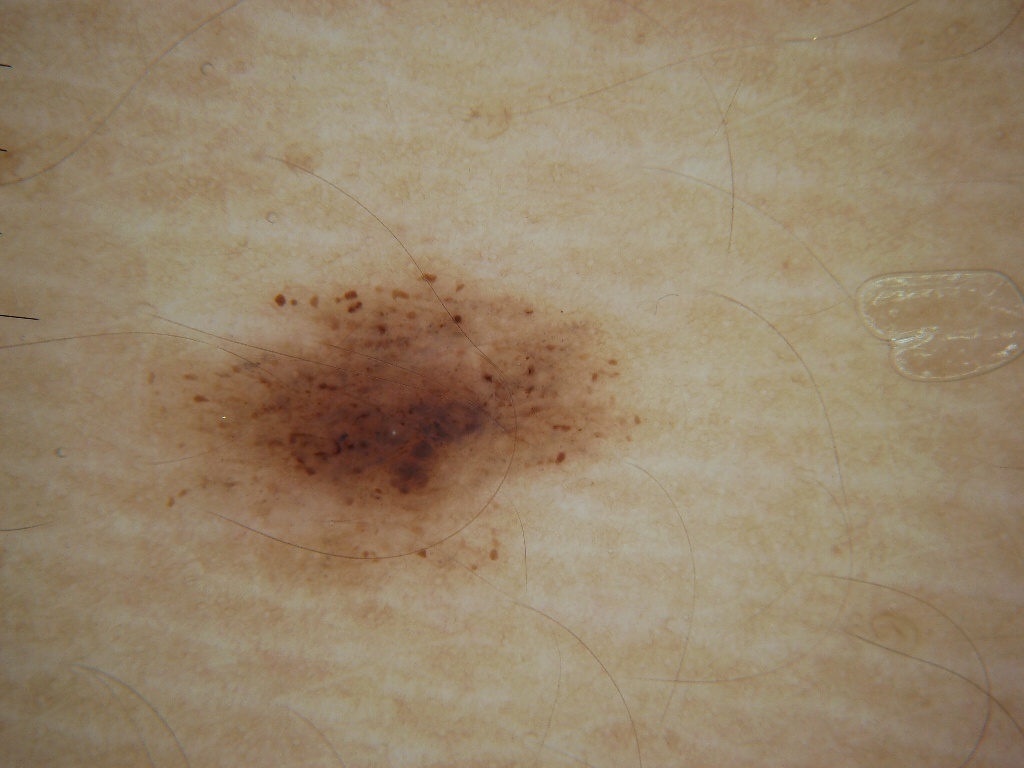A female subject, roughly 30 years of age.
A dermatoscopic image of a skin lesion.
Dermoscopic assessment notes globules, pigment network, and milia-like cysts.
The lesion occupies roughly 18% of the field.
As (left, top, right, bottom), the lesion is located at 136, 256, 663, 599.
Clinically diagnosed as a melanocytic nevus.